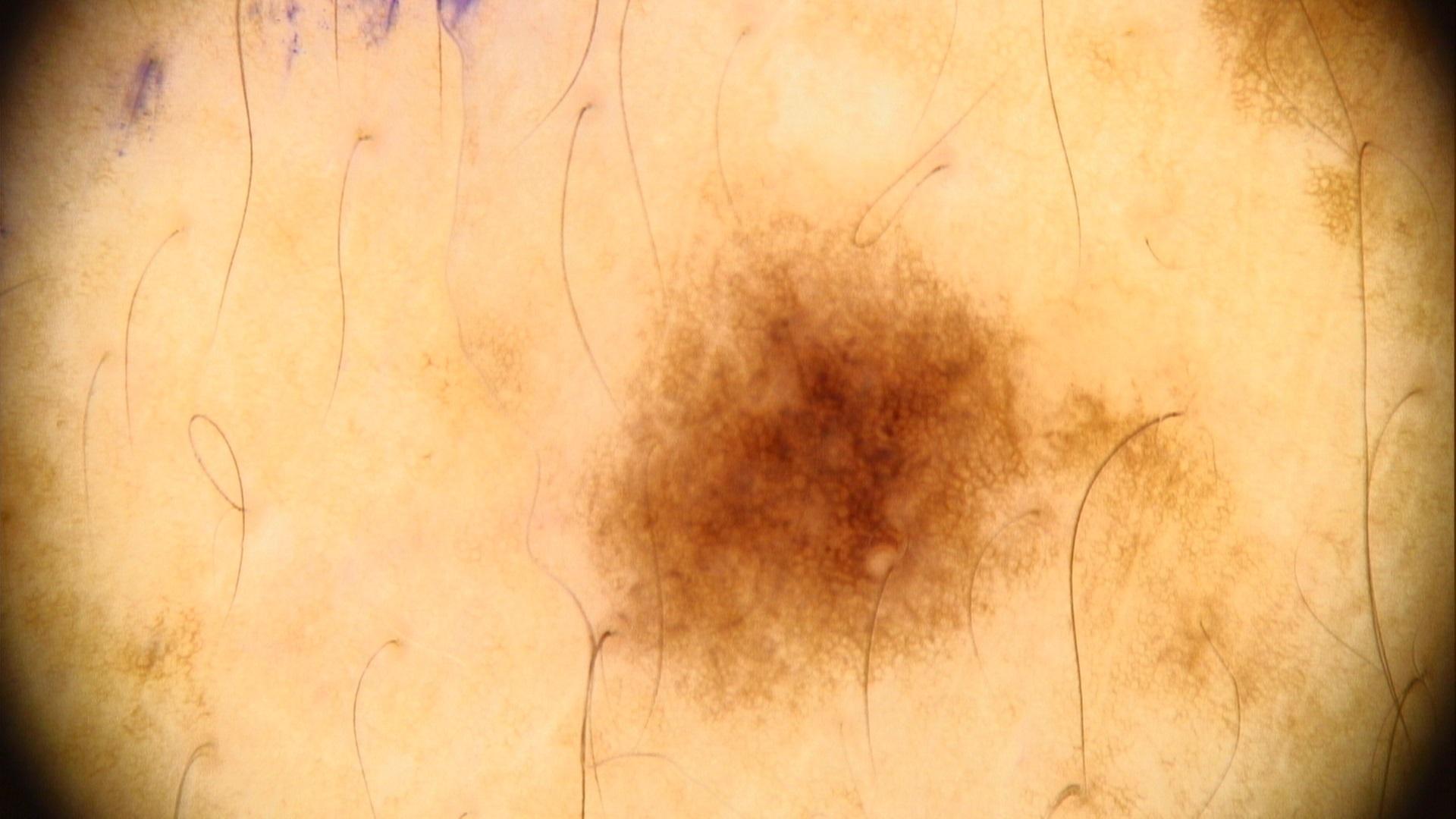Clinical context:
The lesion is located on the trunk, specifically the posterior trunk.
Conclusion:
The clinical assessment was a lesion of melanocytic origin — a nevus.